The patient considered this a rash. Symptoms reported: itching, burning, pain, enlargement, darkening and bothersome appearance. The photograph was taken at an angle. The patient also reports fatigue. The contributor reports the lesion is raised or bumpy. Skin tone: Fitzpatrick II. Located on the top or side of the foot, head or neck, leg and back of the hand. The subject is a female aged 18–29. The contributor reports the condition has been present for one to four weeks: 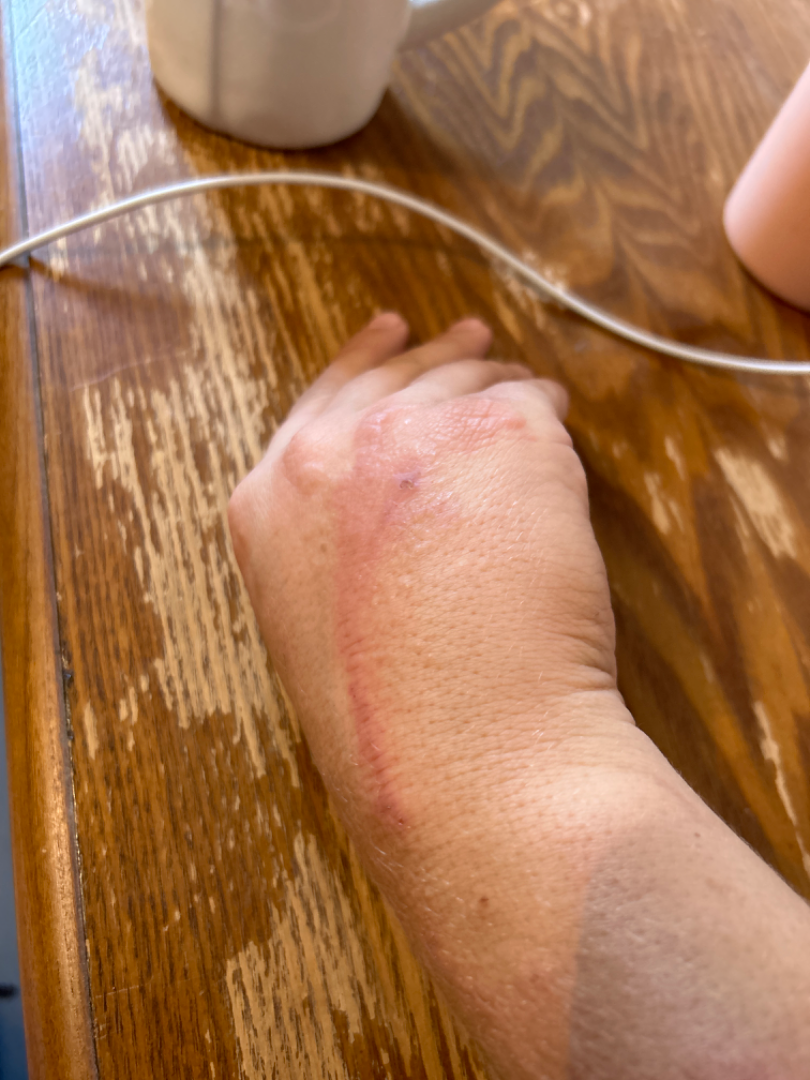On remote dermatologist review: Contact dermatitis (35%); Cat scratch disease (22%); Cutaneous sarcoidosis (22%); Deep fungal infection (22%).